A dermoscopic image of a skin lesion.
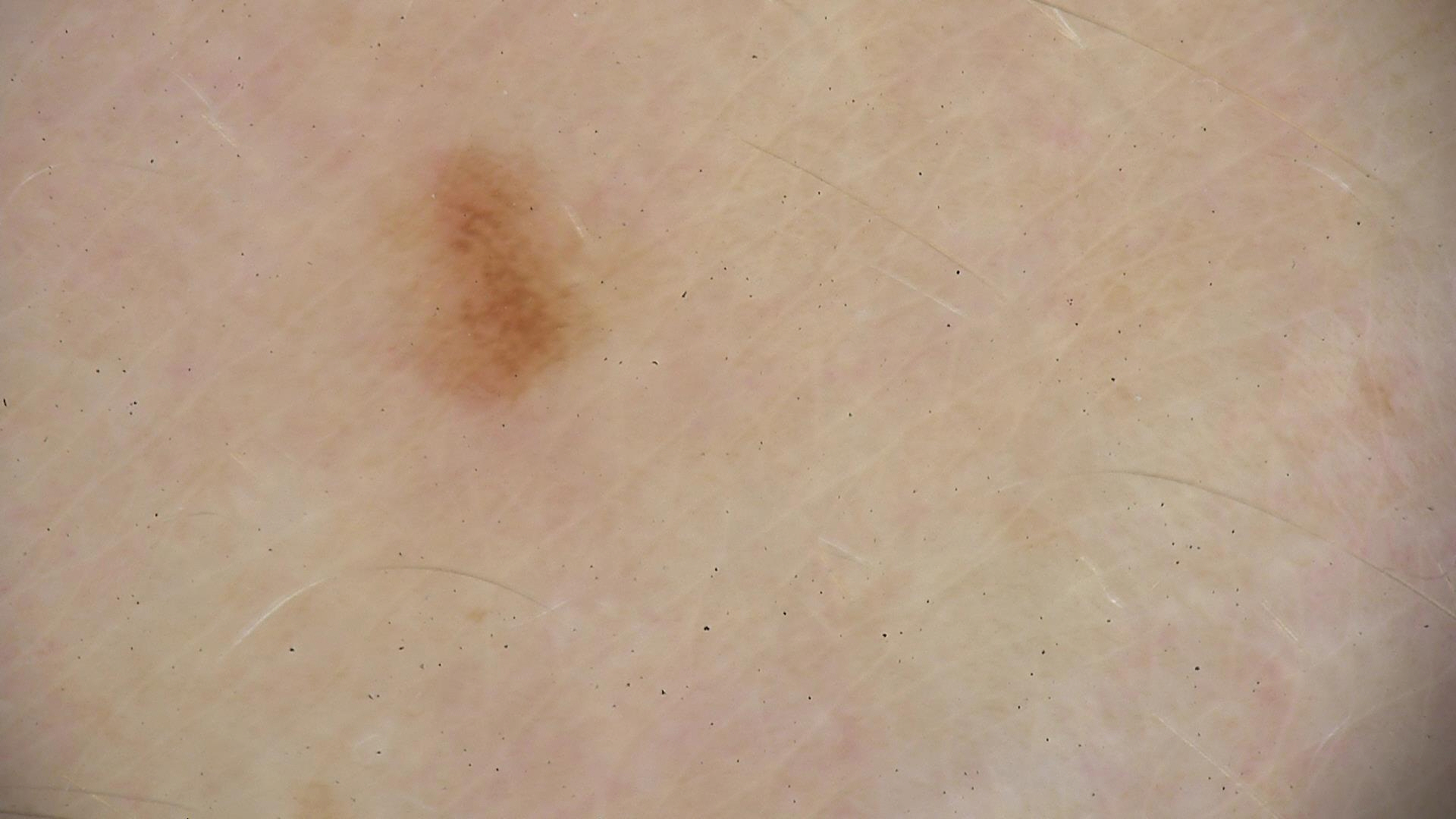Conclusion: The diagnosis was a benign lesion — a dysplastic junctional nevus.